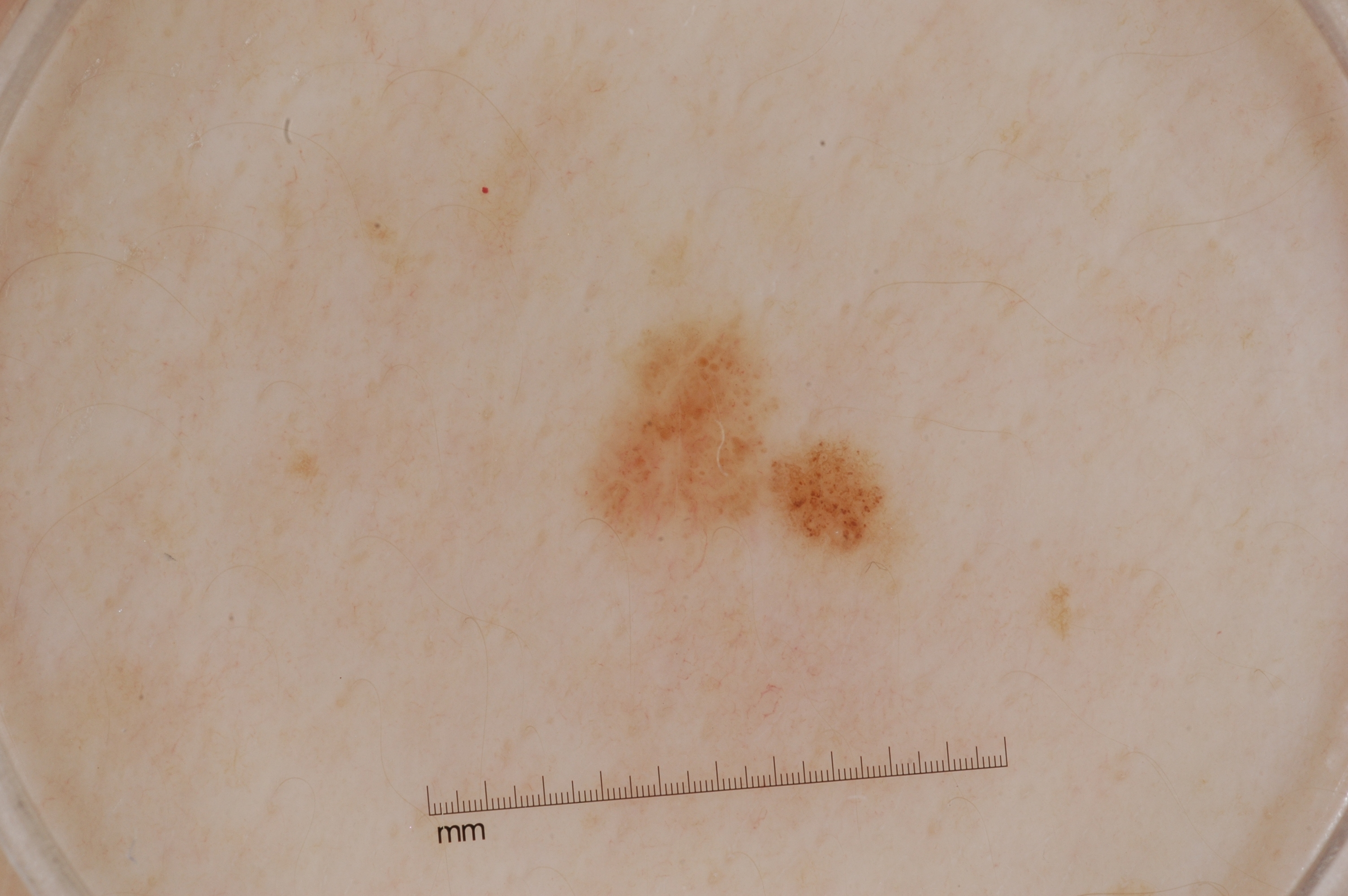Notes:
- image type — dermoscopic image
- patient — female, aged 28-32
- features — milia-like cysts
- lesion size — ~5% of the field
- lesion bbox — (572, 299, 918, 598)
- diagnostic label — a melanocytic nevus